A clinical photo of a skin lesion taken with a smartphone. A female patient 66 years of age. By history, prior skin cancer (patient or family), alcohol use, and prior malignancy (patient or family).
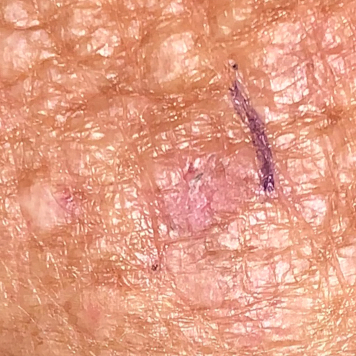Measuring about 8 × 7 mm.
Expert review favored an actinic keratosis.